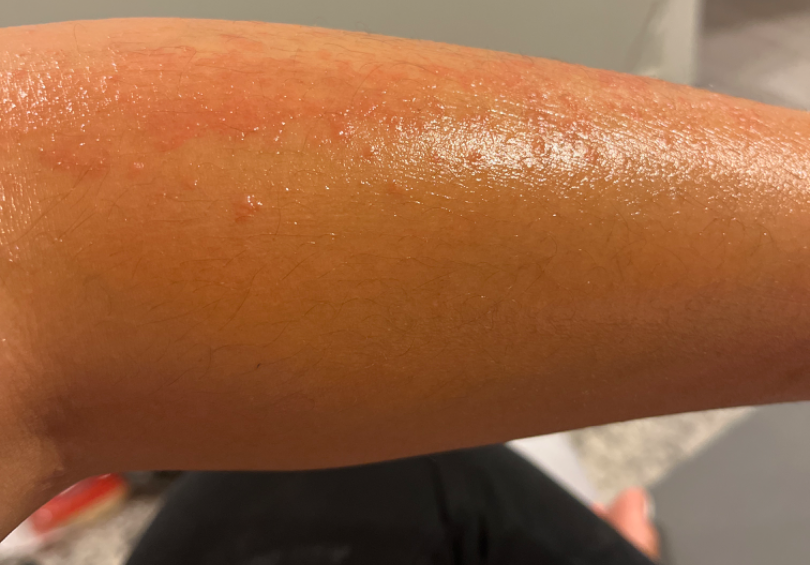Q: How was the photo taken?
A: at an angle
Q: What is the patient's skin tone?
A: FST III
Q: What conditions are considered?
A: Acute dermatitis, NOS (considered); Allergic Contact Dermatitis (considered)